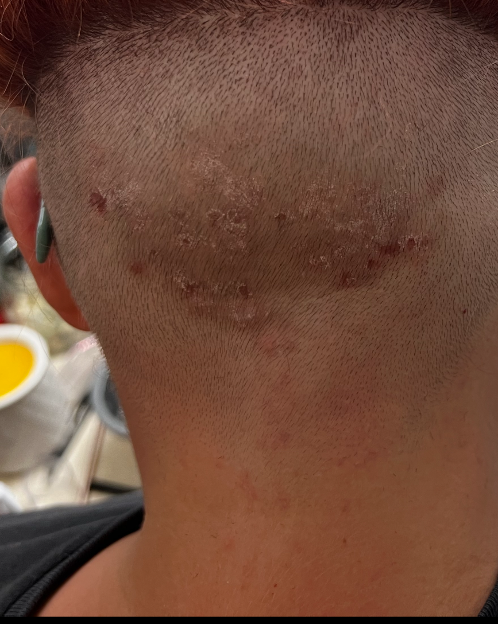differential:
  leading:
    - Acne keloidalis
  considered:
    - Folliculitis decalvans